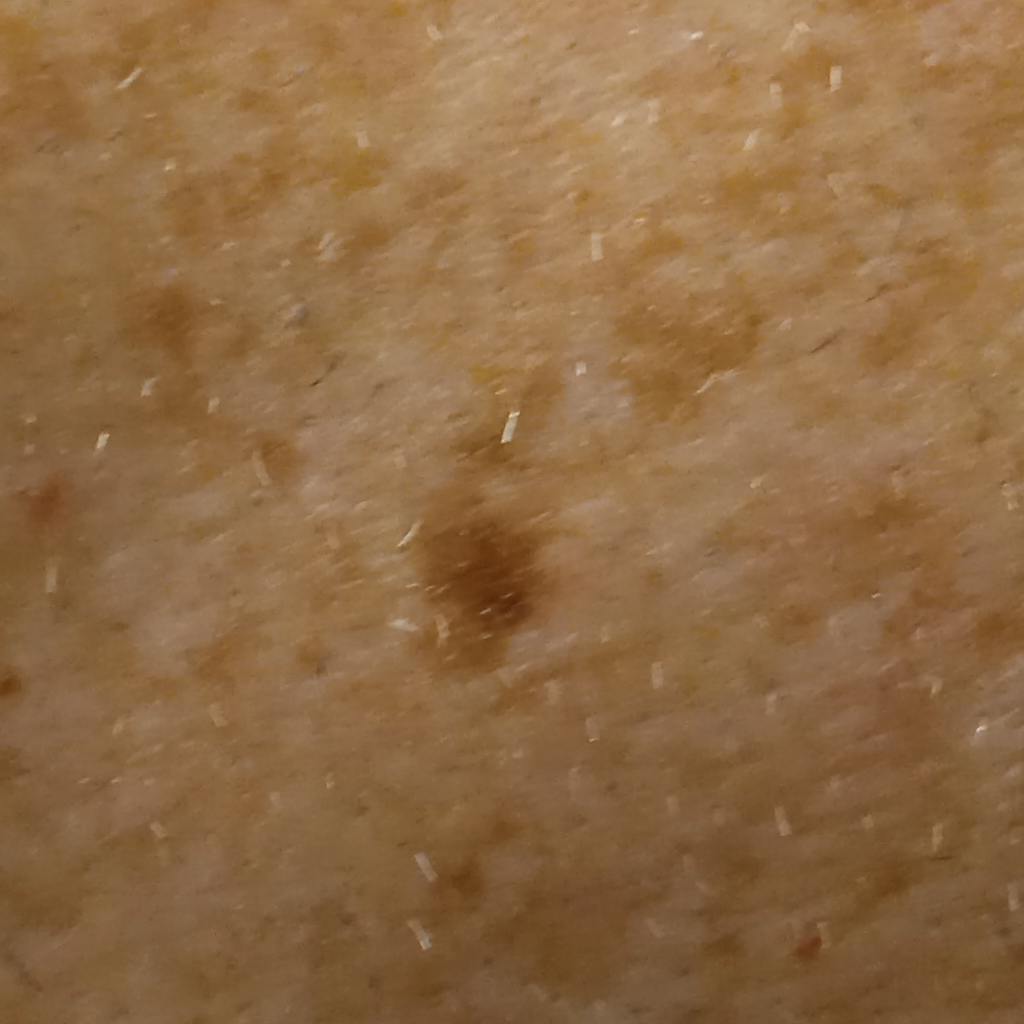Q: What kind of image is this?
A: clinical photo
Q: What is the patient's nevus burden?
A: numerous melanocytic nevi
Q: How does the patient's skin react to sun?
A: skin reddens with sun exposure
Q: What is the referral context?
A: research study (no referral diagnosis)
Q: Tell me about the patient.
A: male, age 73
Q: What are the relevant risk factors?
A: a personal history of cancer, no immunosuppression, no personal history of skin cancer
Q: What is the anatomic site?
A: the torso
Q: Lesion size?
A: 6.6 mm
Q: What was the diagnosis?
A: melanoma (dermatologist consensus)